A skin lesion imaged with a dermatoscope · the chart notes melanoma in a first-degree relative but no prior melanoma · the patient was assessed as Fitzpatrick skin type III · a male patient roughly 40 years of age: 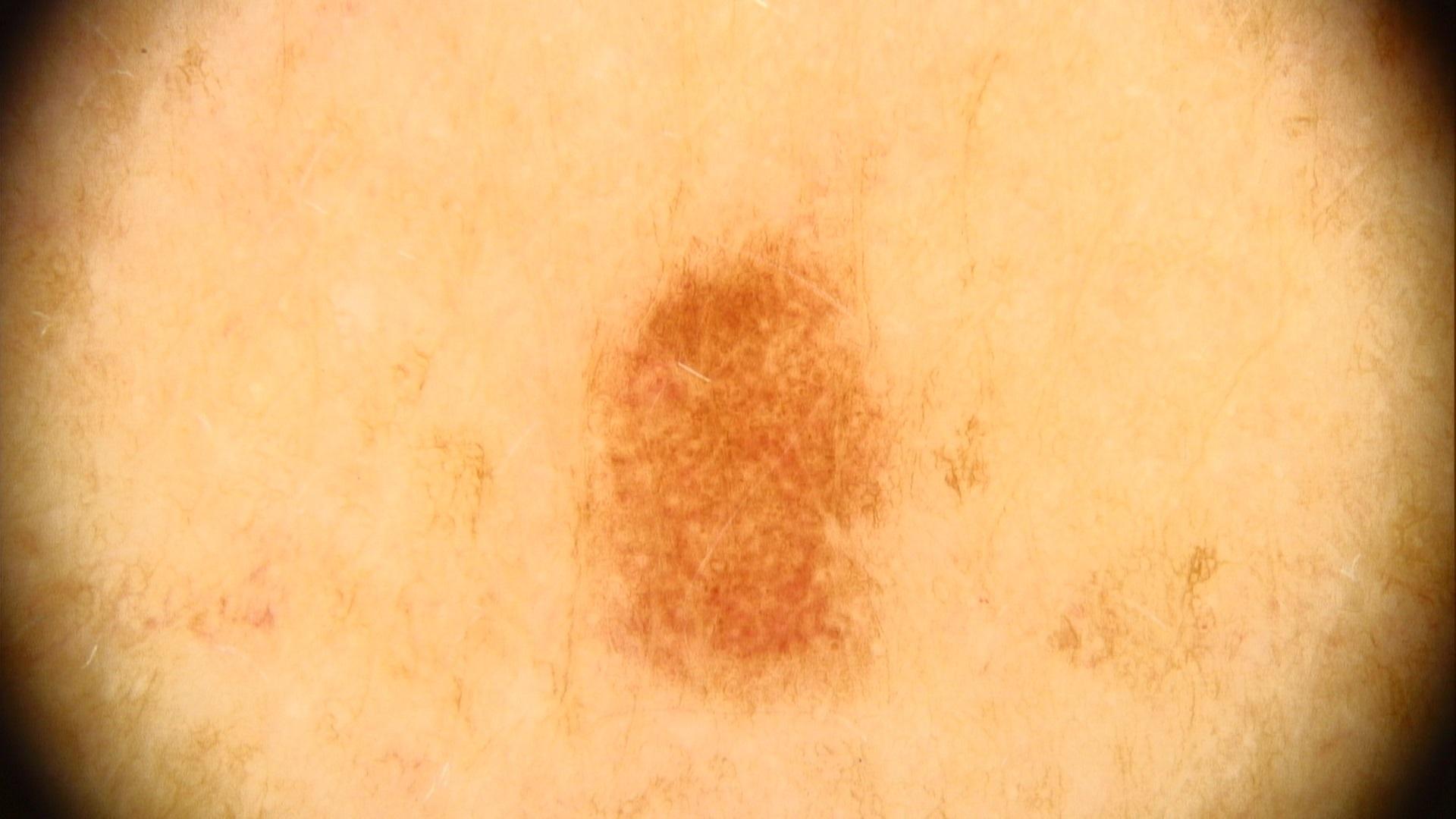{"lesion_location": {"region": "the trunk", "detail": "the posterior trunk"}, "diagnosis": {"name": "Nevus", "malignancy": "benign", "confirmation": "expert clinical impression", "lineage": "melanocytic"}}